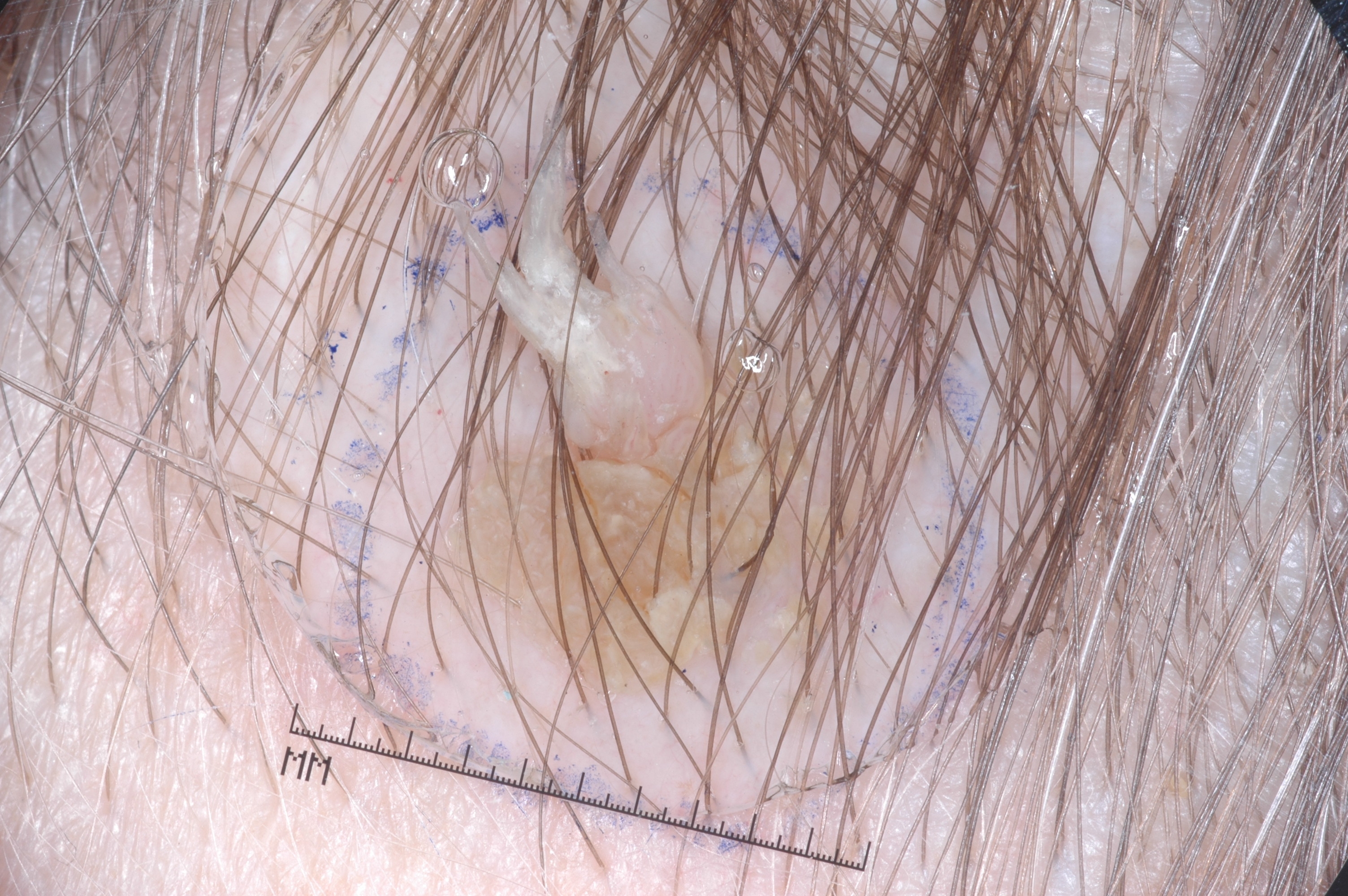A dermatoscopic image of a skin lesion.
The subject is a female aged 43-47.
The lesion is bounded by x1=427 y1=93 x2=945 y2=705.
Dermoscopy demonstrates no milia-like cysts, negative network, pigment network, or streaks.
The diagnostic assessment was a seborrheic keratosis, a keratinocytic lesion.